The arm is involved, an image taken at a distance:
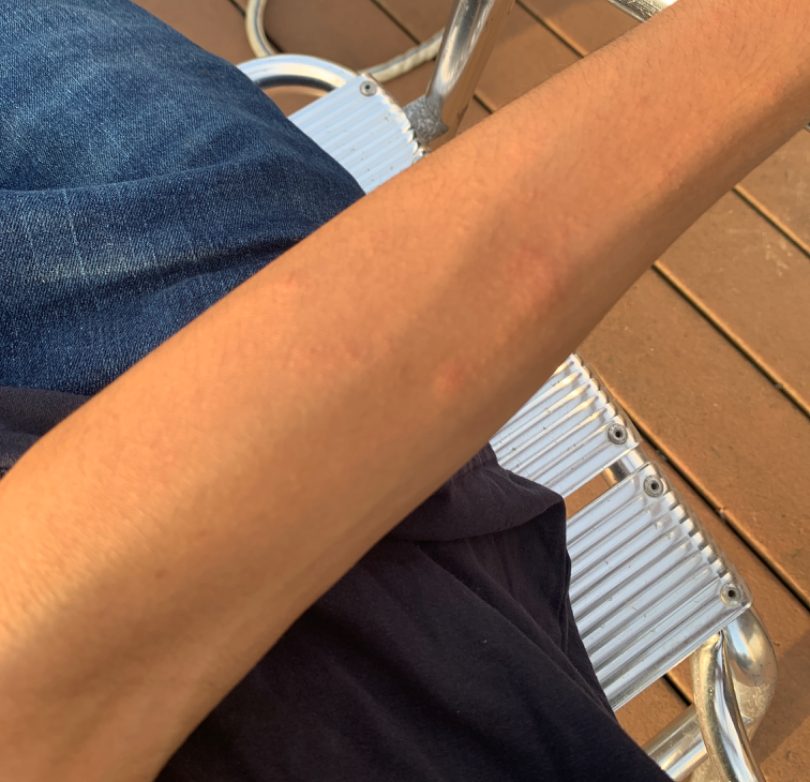The reviewer was unable to grade this case for skin condition. The patient described the issue as a rash. The lesion is described as raised or bumpy.